The affected area is the arm. Female subject, age 40–49. A close-up photograph:
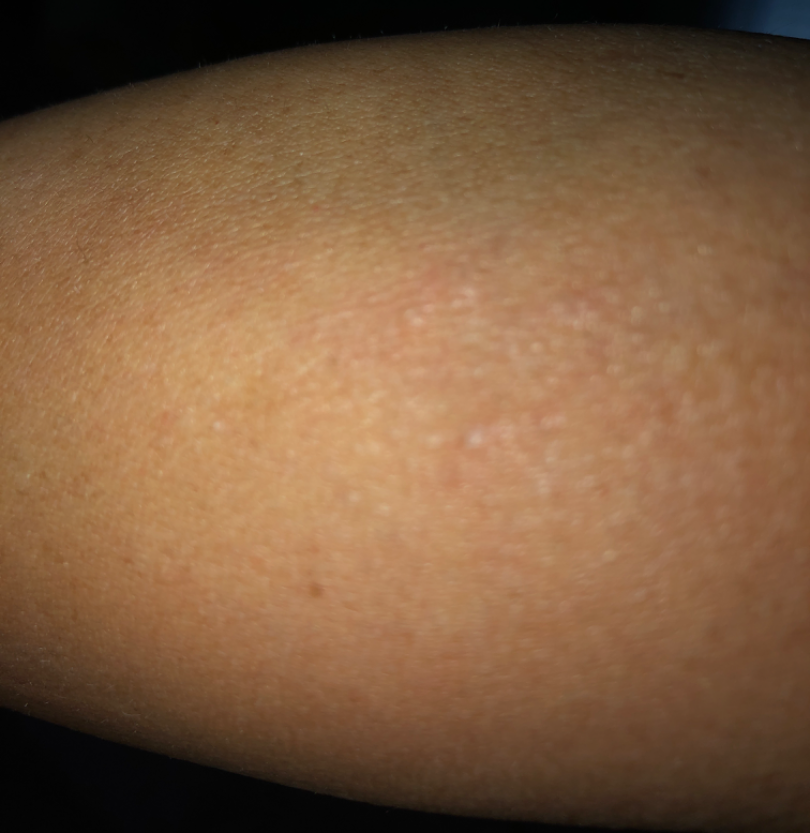The contributor notes associated fever. Reported duration is one to four weeks. The patient considered this a rash. The contributor notes itching. The favored diagnosis is Eczema; an alternative is Lichenoid myxedema; also consider Discrete papular lichen myxedematosus.